A clinical photograph of a skin lesion · the patient says their skin reddens with sun exposure · the patient describes having few moles overall · a female patient 15 years old · referred with a clinical suspicion of melanocytic nevus — 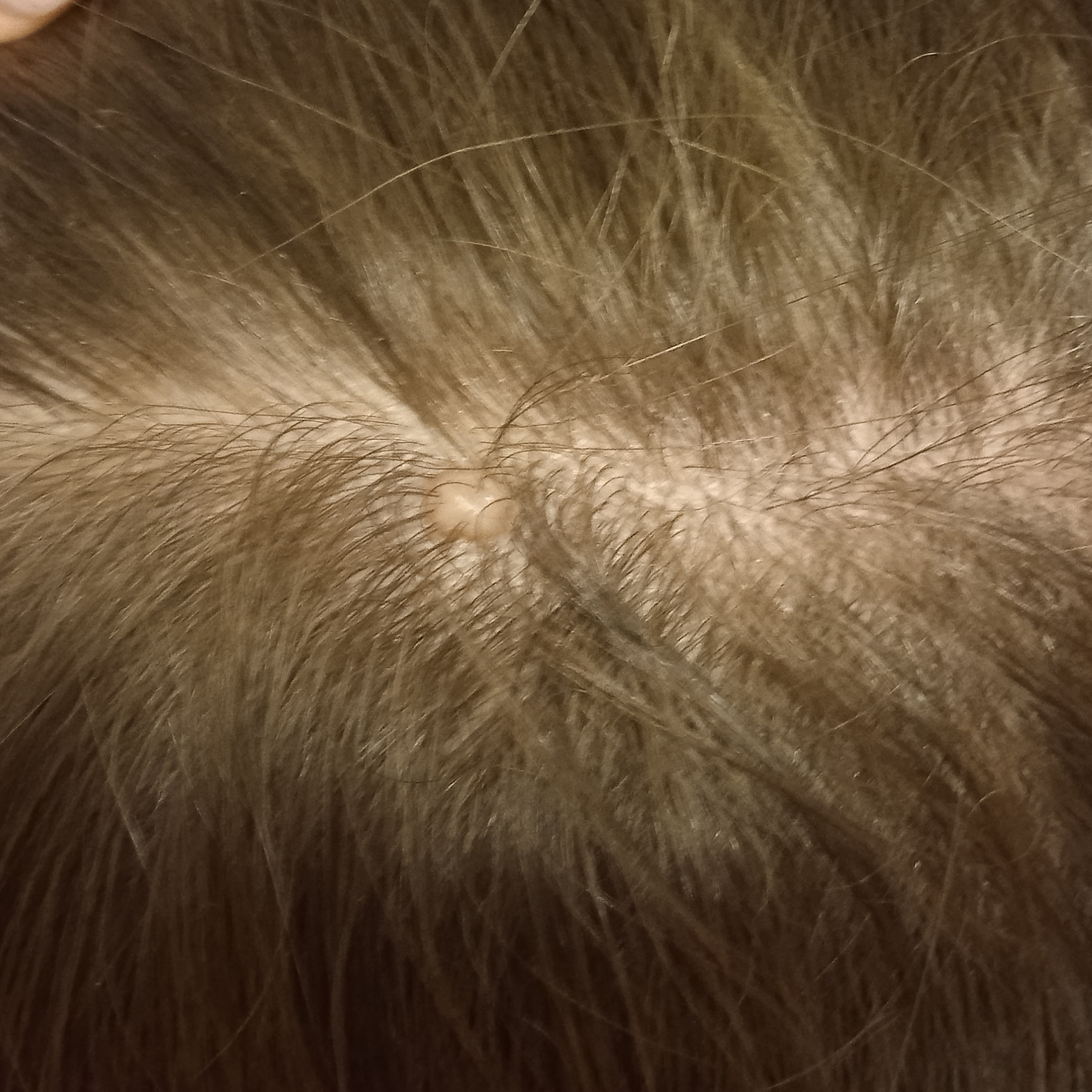The lesion involves the head.
Measuring roughly 5 mm.
Confirmed on histopathology as a melanocytic nevus, following excision.